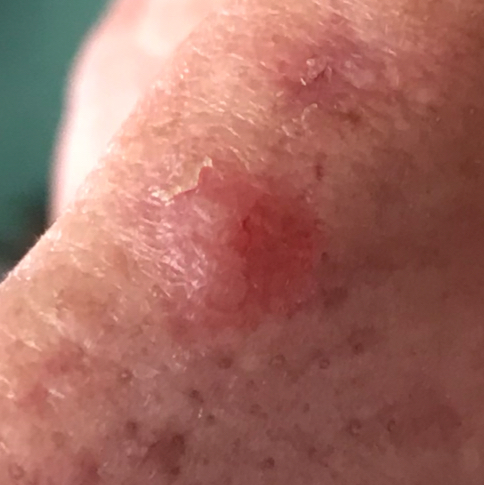Patient and lesion: A clinical photograph showing a skin lesion. The patient reports that the lesion has bled, has grown, is elevated, itches, and hurts. Pathology: Biopsy-confirmed as a basal cell carcinoma.